The lesion involves the leg, the subject is a female aged 18–29, the photo was captured at an angle — 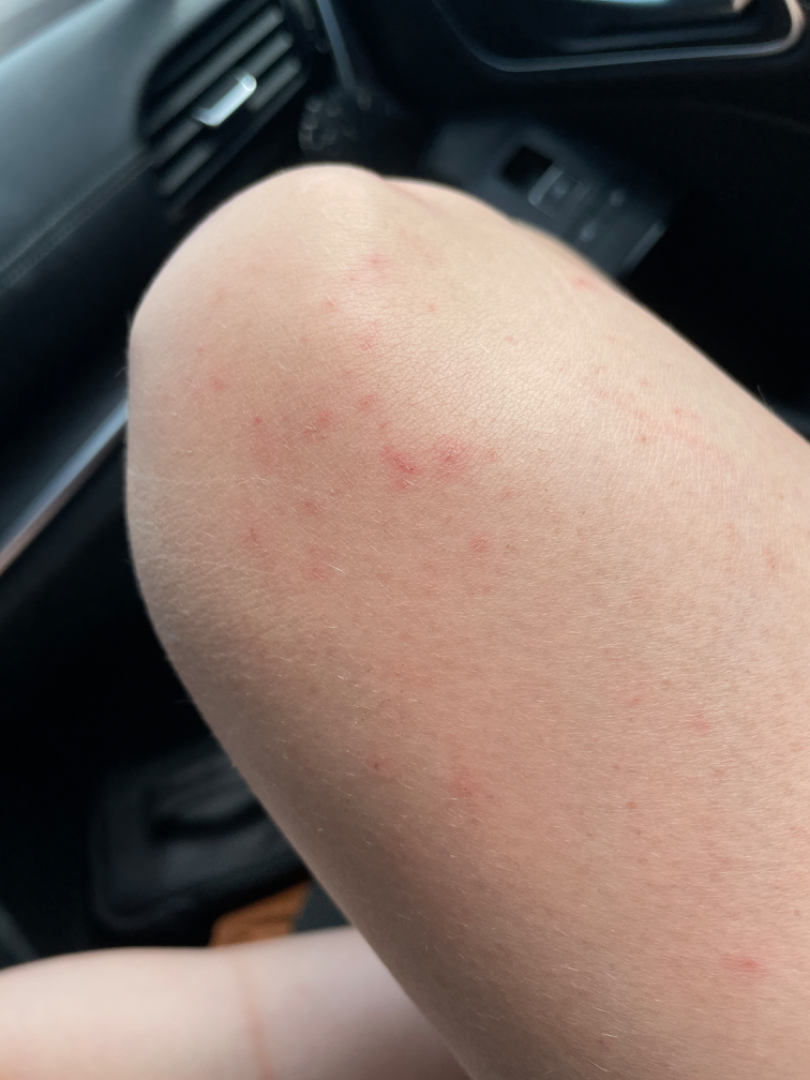<dermatology_case>
  <patient_category>a rash</patient_category>
  <skin_tone>
    <monk_skin_tone>2</monk_skin_tone>
  </skin_tone>
  <duration>less than one week</duration>
  <texture>raised or bumpy</texture>
  <symptoms>enlargement, burning</symptoms>
  <differential>
    <leading>Folliculitis</leading>
    <considered>Eczema</considered>
  </differential>
</dermatology_case>